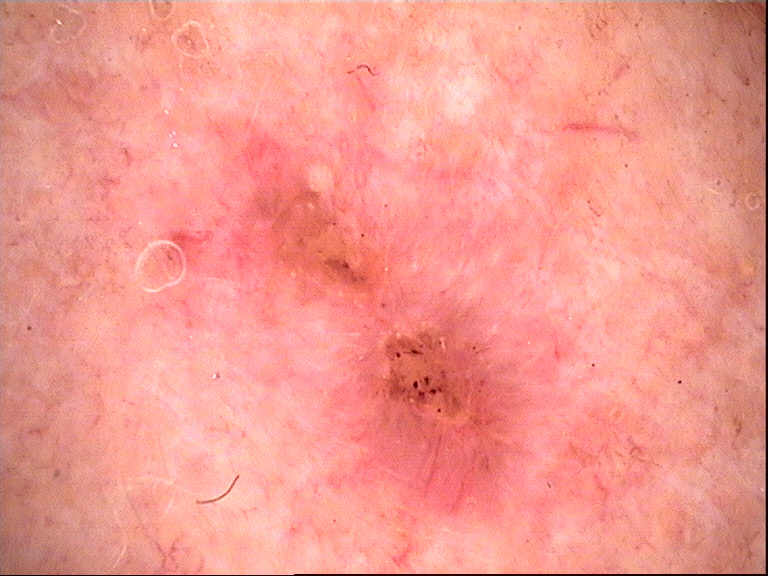Case:
• diagnostic label: basal cell carcinoma (biopsy-proven)